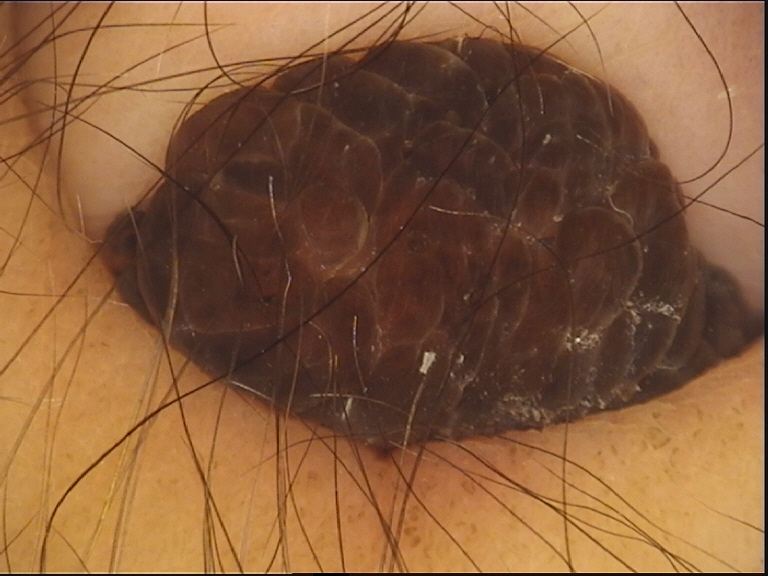image = dermoscopy
category = banal
assessment = dermal nevus (expert consensus)